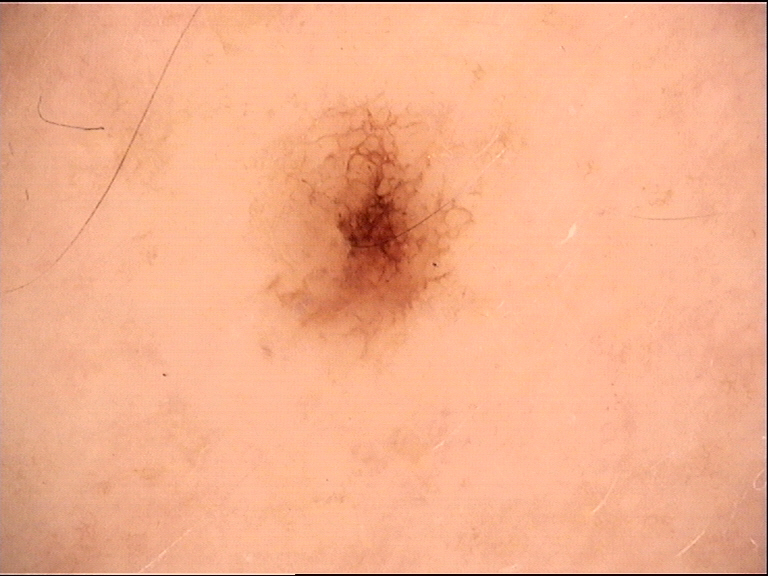A dermoscopic photograph of a skin lesion. Diagnosed as a benign lesion — a dysplastic junctional nevus.